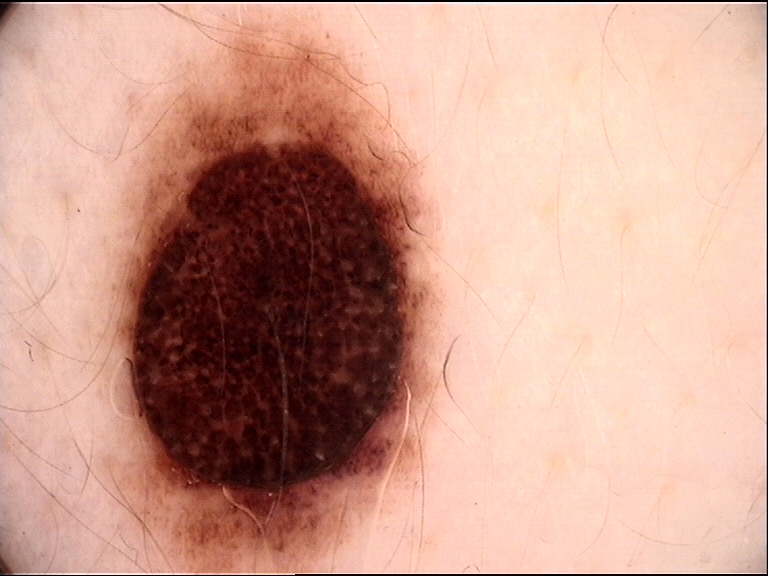Consistent with a dysplastic compound nevus.